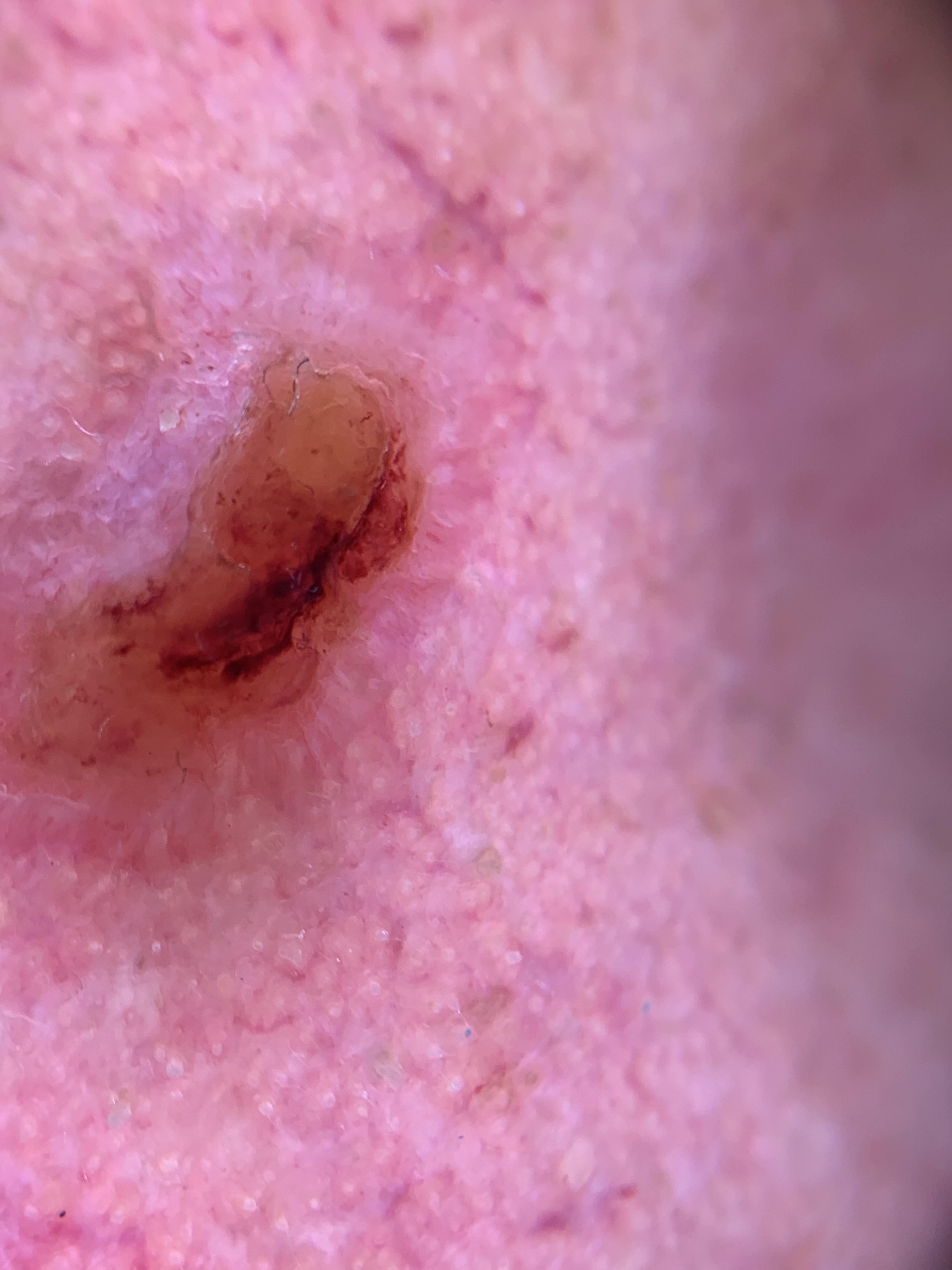Biopsy-confirmed as a basal cell carcinoma.